A female patient, aged around 70; a dermatoscopic image of a skin lesion.
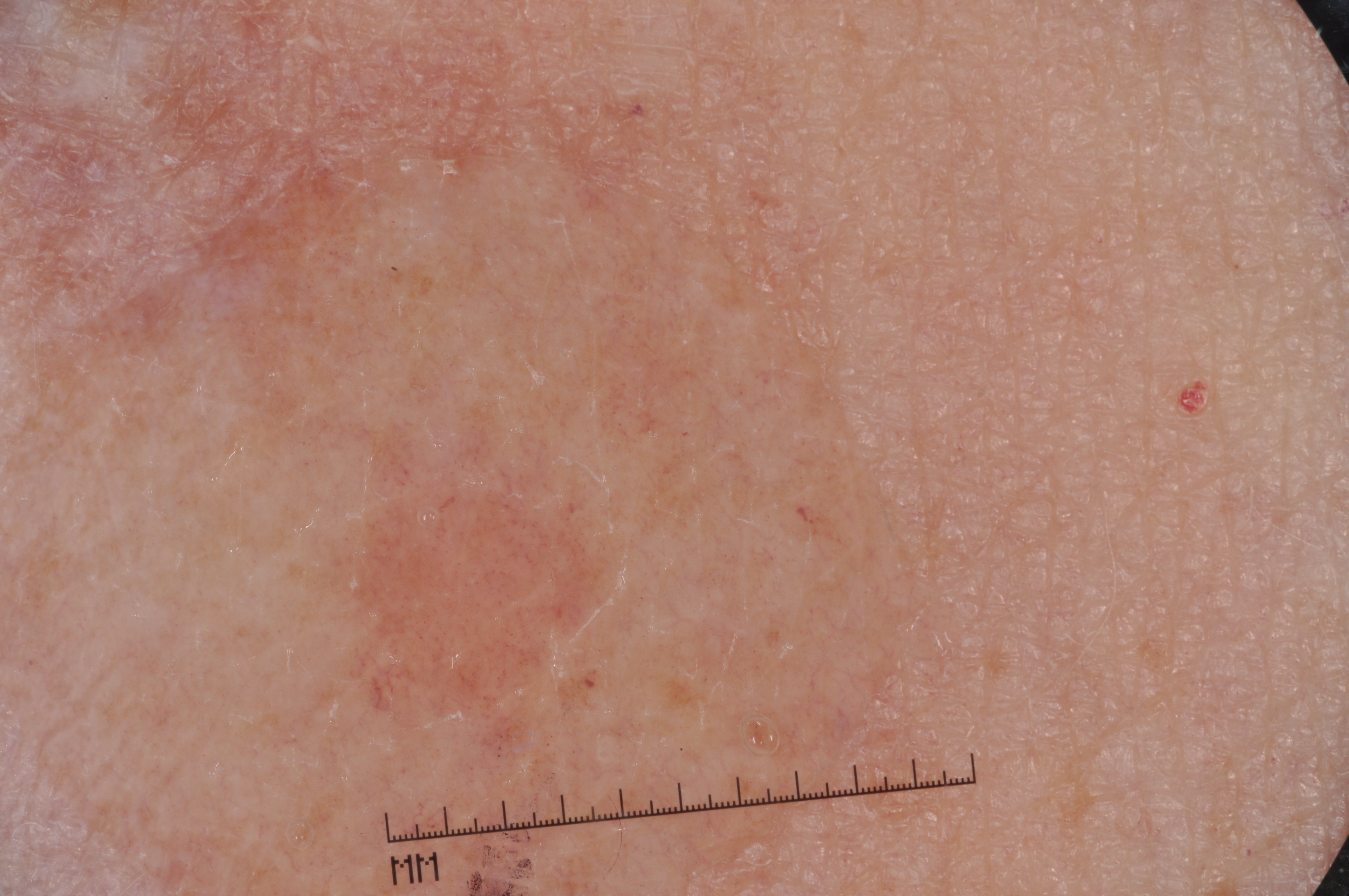Dermoscopic examination shows no pigment network, milia-like cysts, streaks, or negative network. The lesion spans bbox=[309, 416, 621, 747]. The clinical diagnosis was a melanocytic nevus, a benign skin lesion.